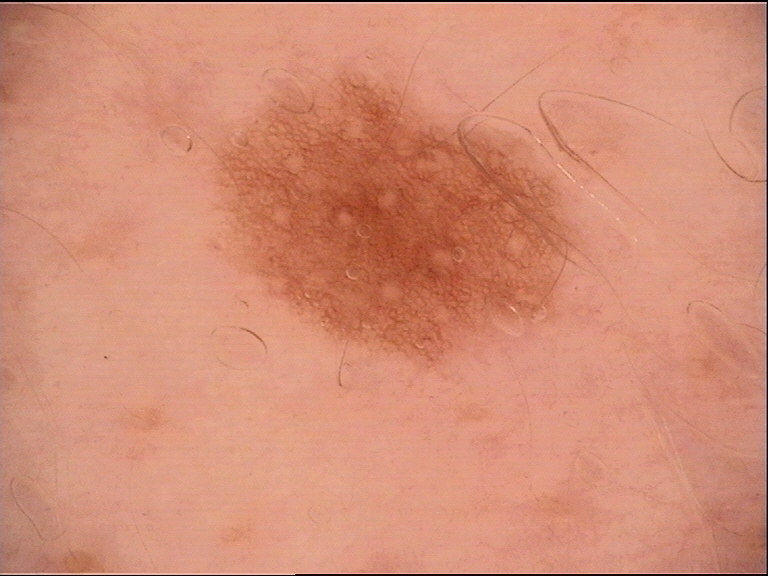image type=dermoscopy; label=dysplastic junctional nevus (expert consensus).